A male subject in their late 40s; a clinical photo of a skin lesion taken with a smartphone:
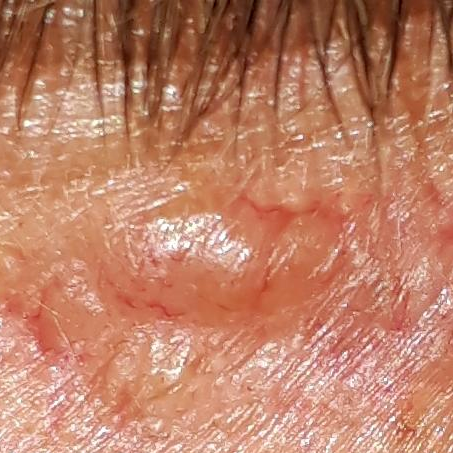region: the face
diagnosis: basal cell carcinoma (biopsy-proven)